The patient notes associated fever · female subject, age 18–29 · an image taken at an angle · reported lesion symptoms include itching, pain and bothersome appearance · the patient considered this a rash · the patient notes the lesion is raised or bumpy and fluid-filled · the lesion involves the leg — 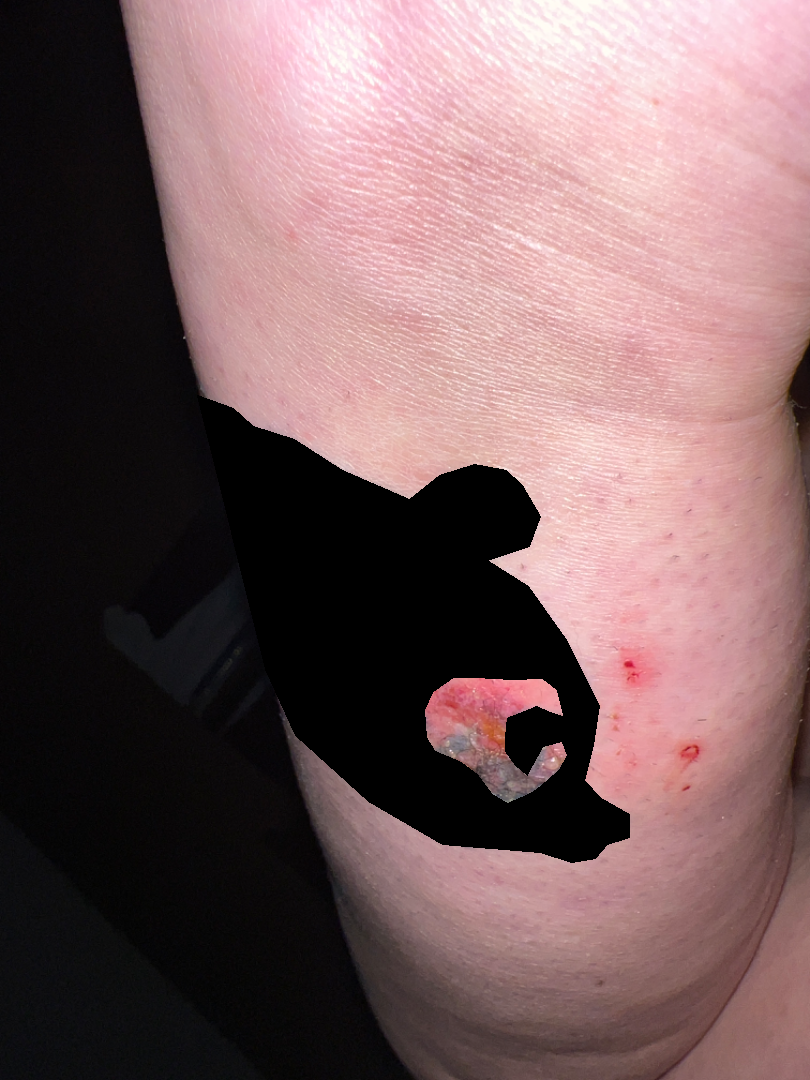Q: Could the case be diagnosed?
A: indeterminate